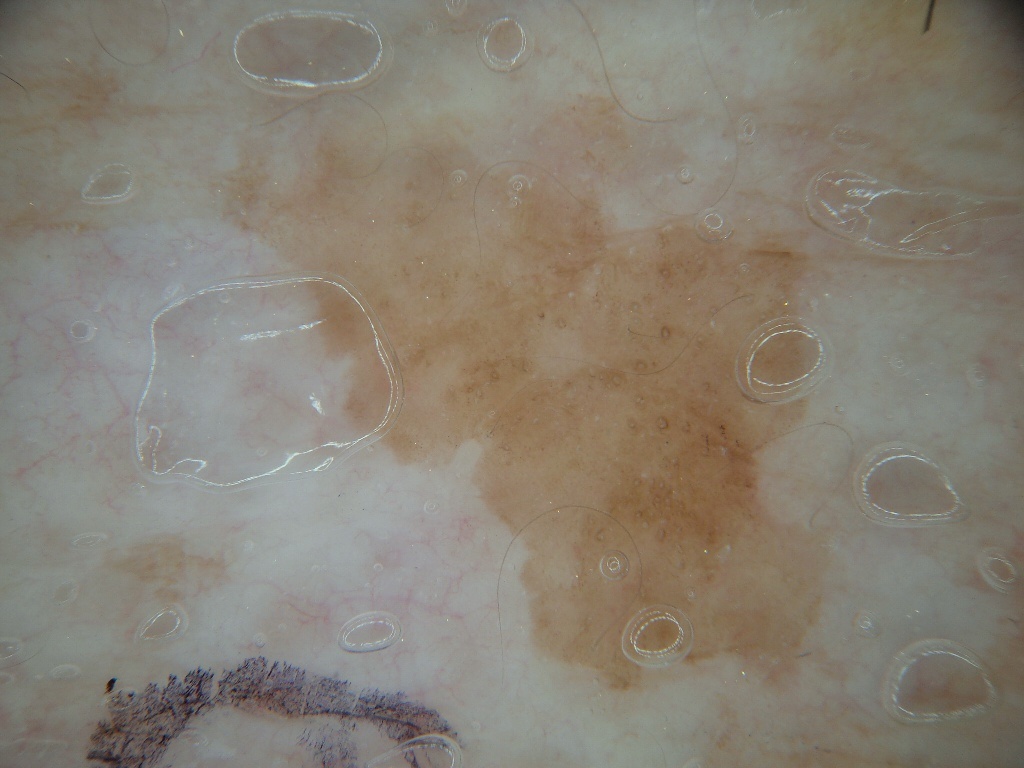Case summary:
- image type — dermoscopic image
- bounding box — x1=197, y1=92, x2=864, y2=716
- impression — a benign skin lesion